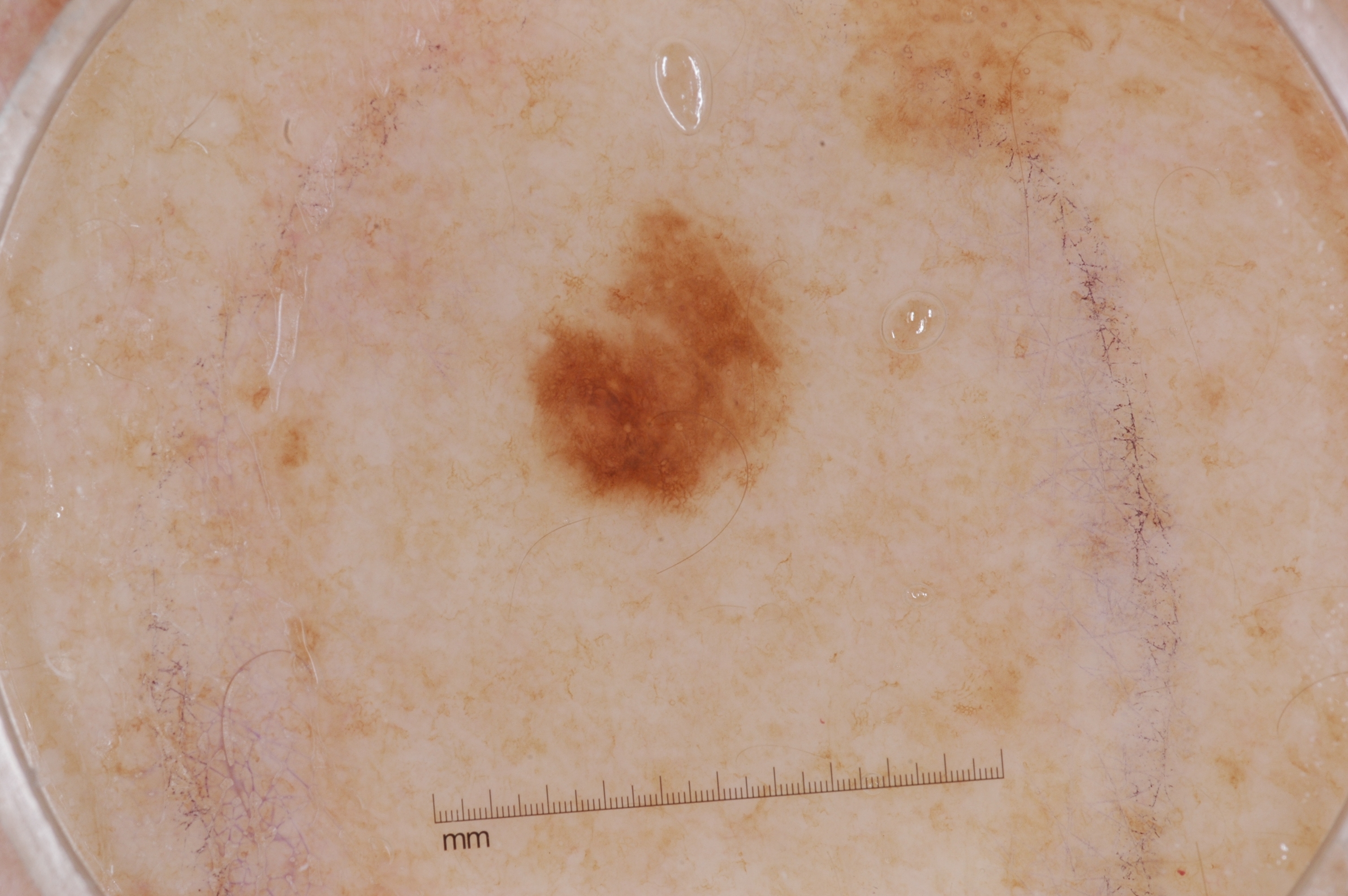Image and clinical context:
A dermoscopy image of a single skin lesion. The subject is a female in their mid- to late 60s. In (x1, y1, x2, y2) order, the visible lesion spans [527, 217, 790, 511]. Dermoscopically, the lesion shows pigment network, with no negative network, milia-like cysts, or streaks.
Conclusion:
The diagnostic assessment was a melanocytic nevus.